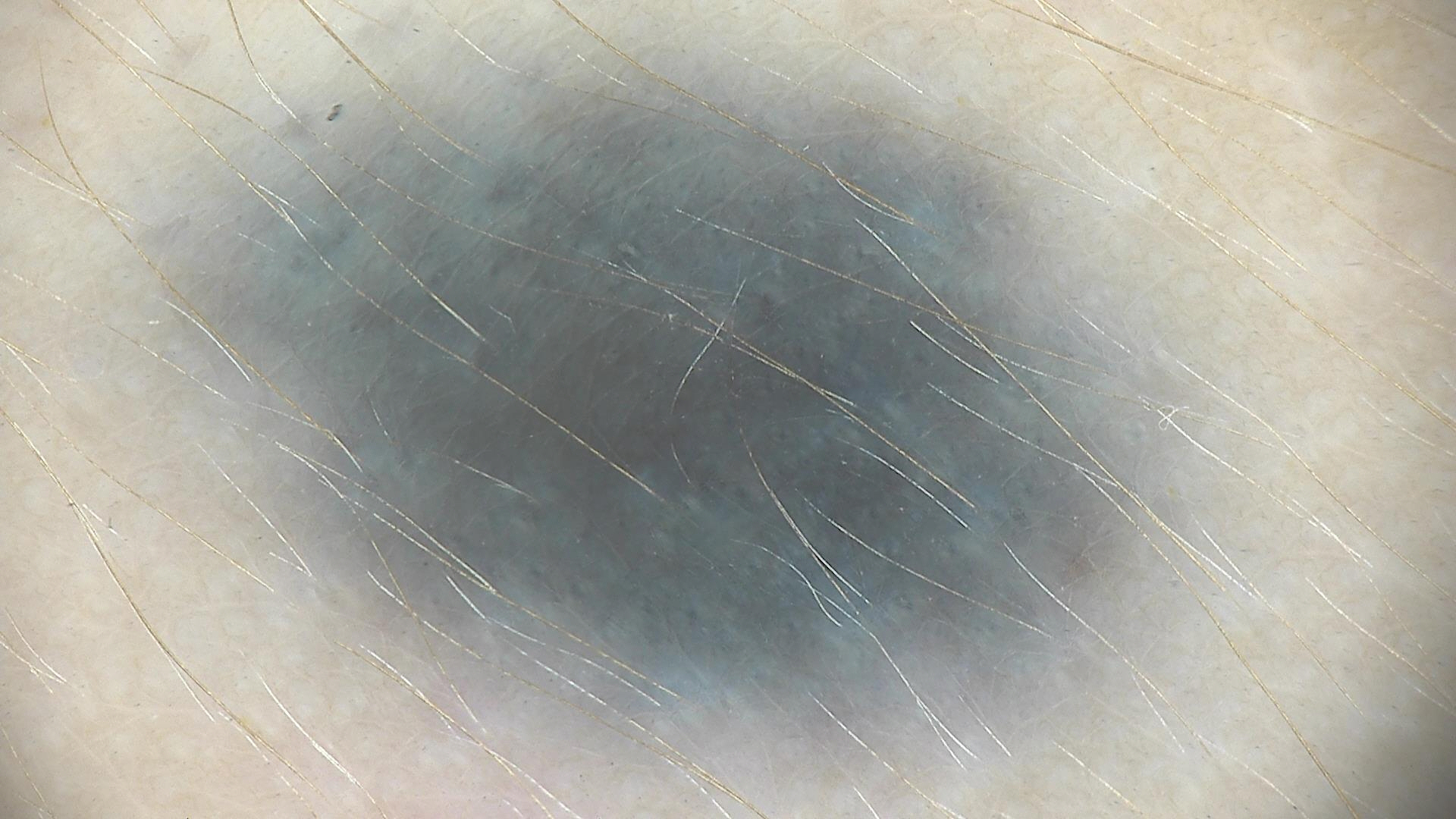modality = dermoscopy; subtype = banal, dermal; class = blue nevus (expert consensus).